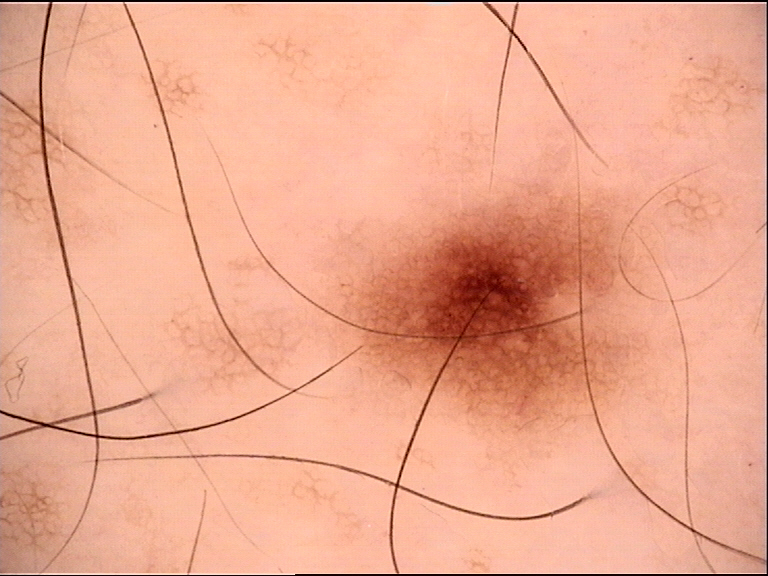| field | value |
|---|---|
| image type | dermoscopy |
| diagnosis | junctional nevus (expert consensus) |